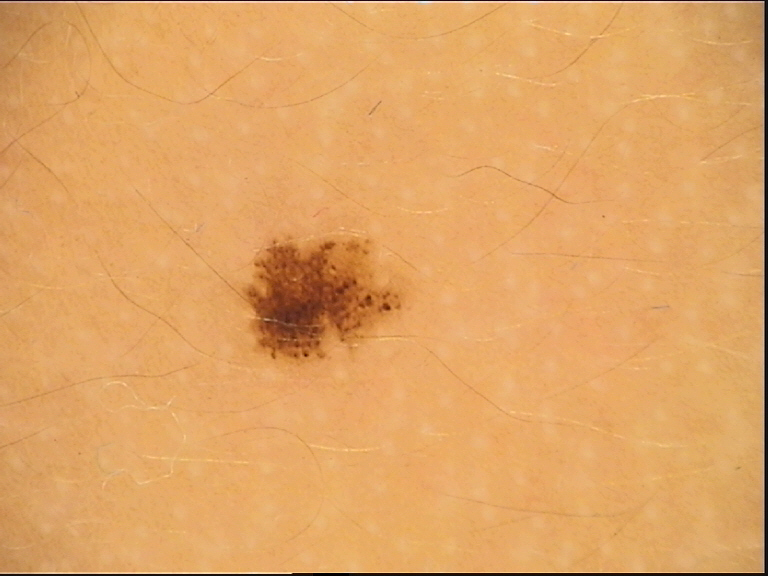Labeled as a benign lesion — a dysplastic junctional nevus.